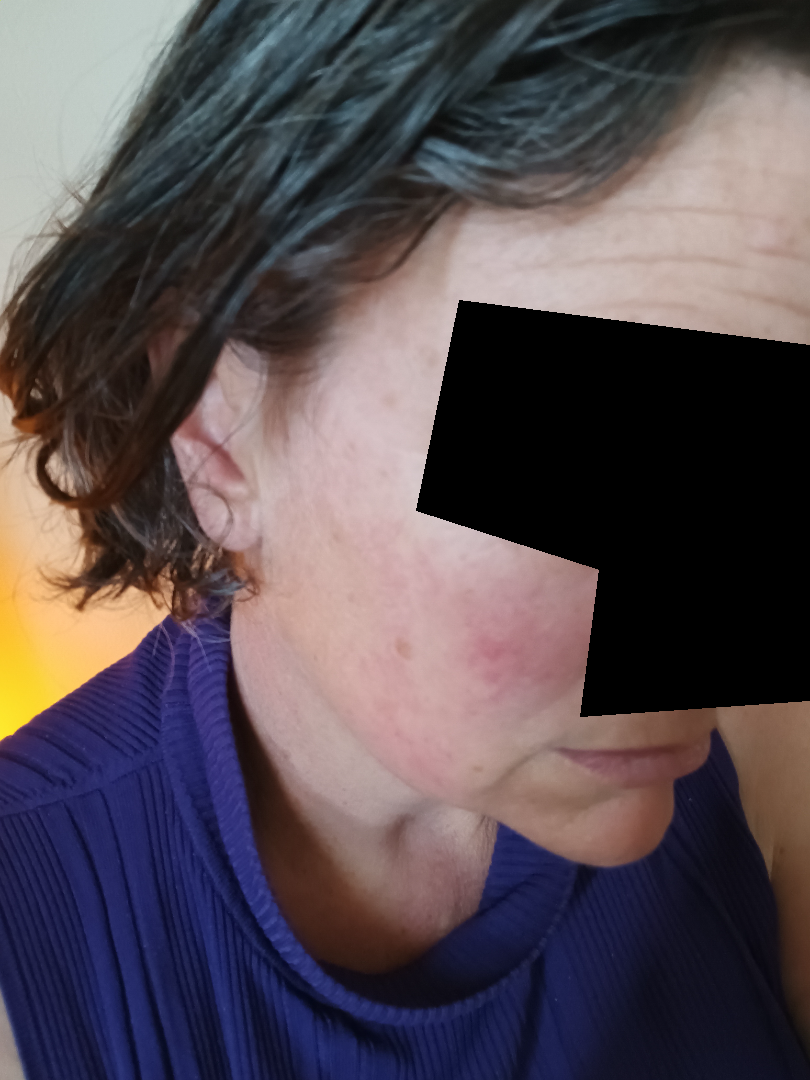| field | value |
|---|---|
| image framing | at a distance |
| systemic symptoms | fatigue, mouth sores and joint pain |
| symptom duration | more than five years |
| symptoms | enlargement, burning, bothersome appearance, pain, itching and darkening |
| self-categorized as | a rash |
| patient | female, age 40–49 |
| lesion texture | flat, raised or bumpy and rough or flaky |